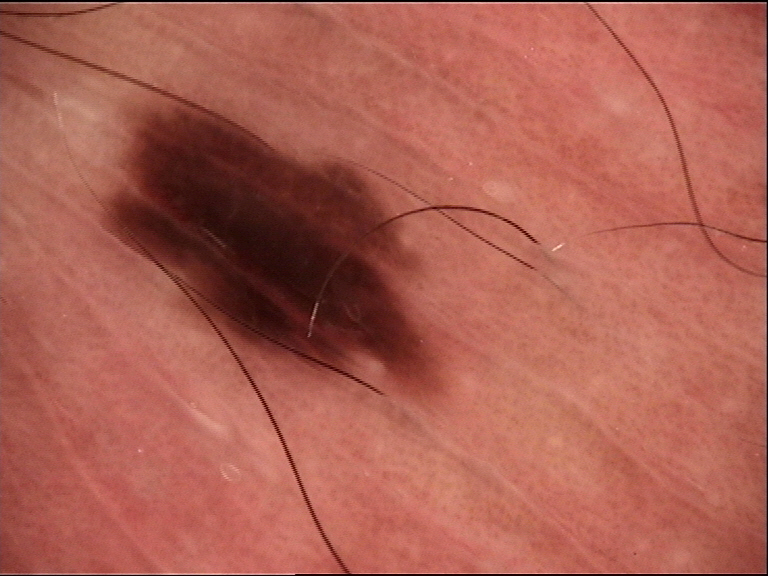A dermoscopy image of a single skin lesion. Consistent with a dysplastic junctional nevus.